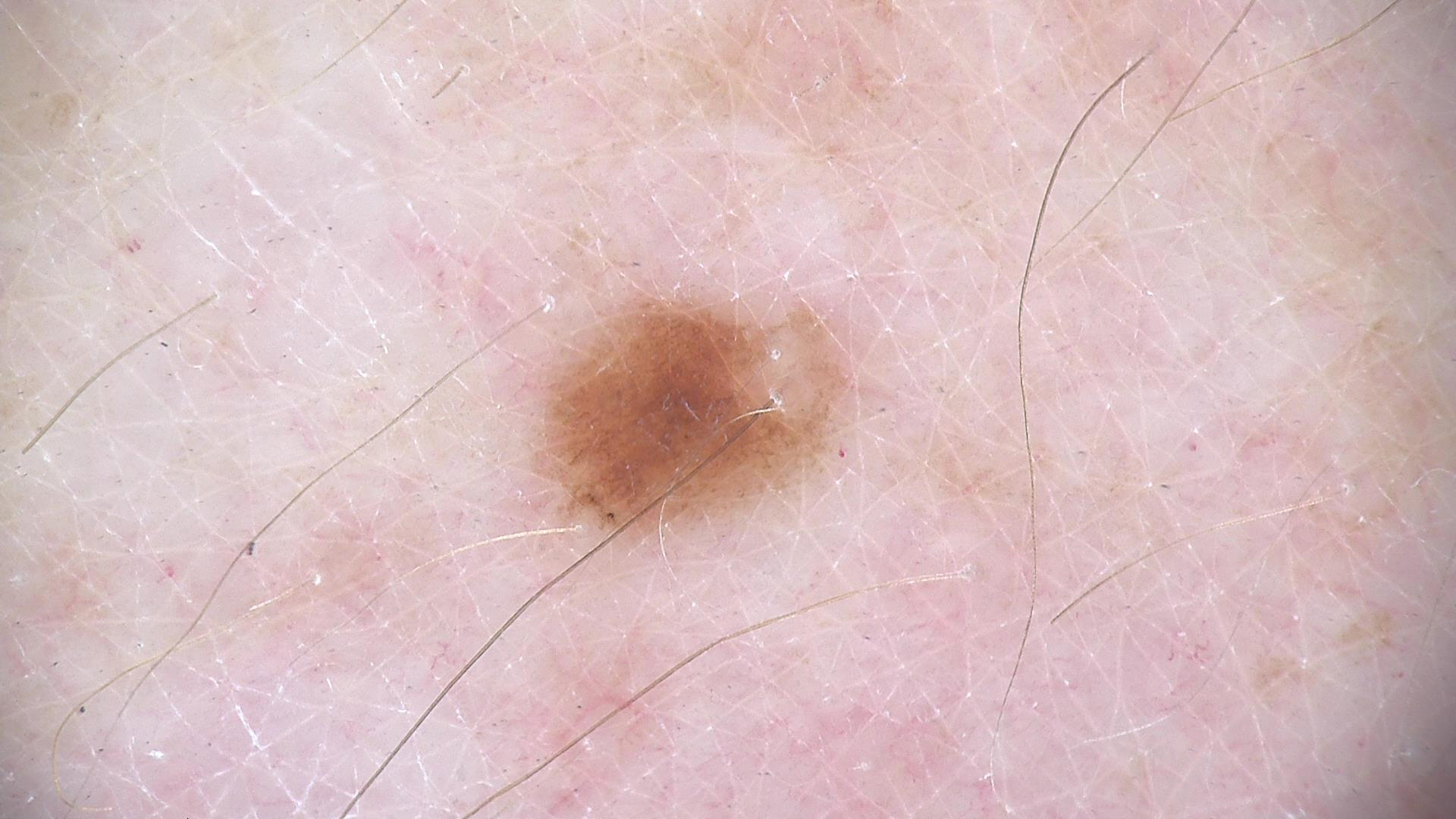{
  "image": "dermatoscopy",
  "diagnosis": {
    "name": "dysplastic junctional nevus",
    "code": "jd",
    "malignancy": "benign",
    "super_class": "melanocytic",
    "confirmation": "expert consensus"
  }
}